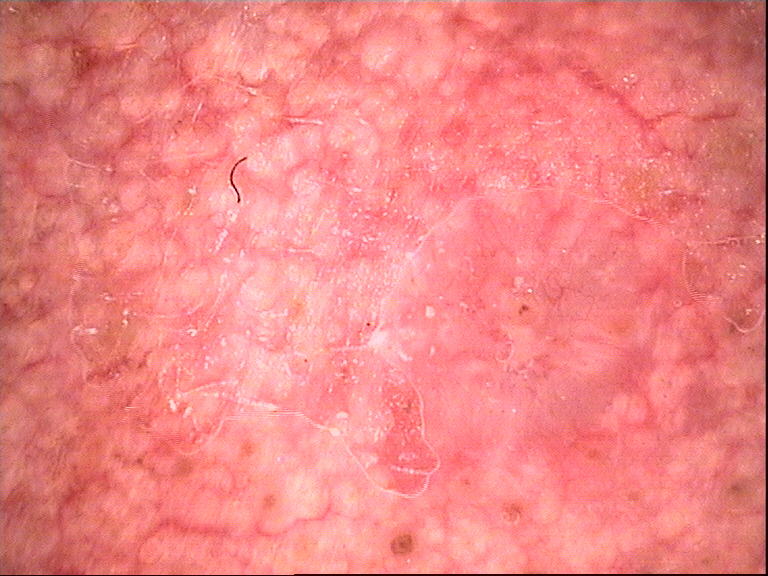Conclusion: Biopsy-confirmed as a keratinocytic lesion — a basal cell carcinoma.